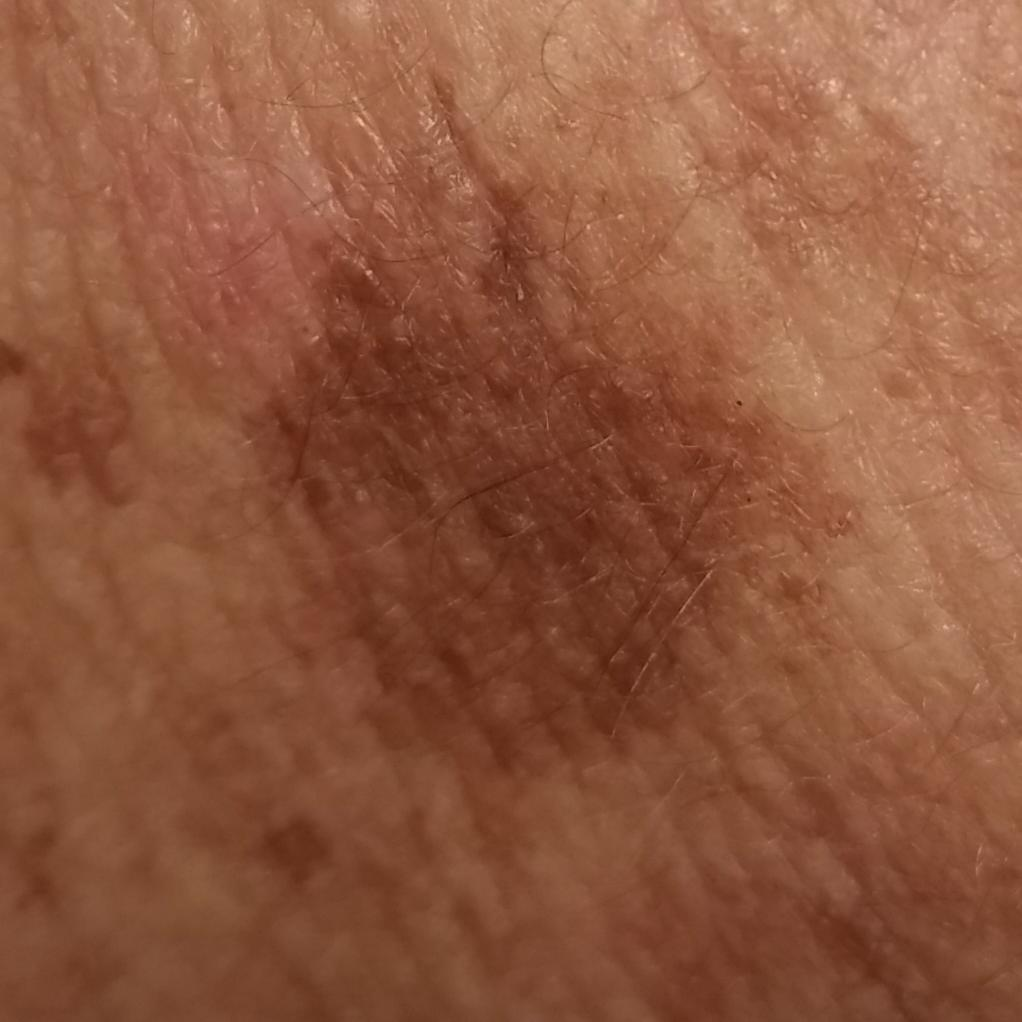Conclusion: The clinical impression was a seborrheic keratosis.